A skin lesion imaged with a dermatoscope · a female subject in their 50s — 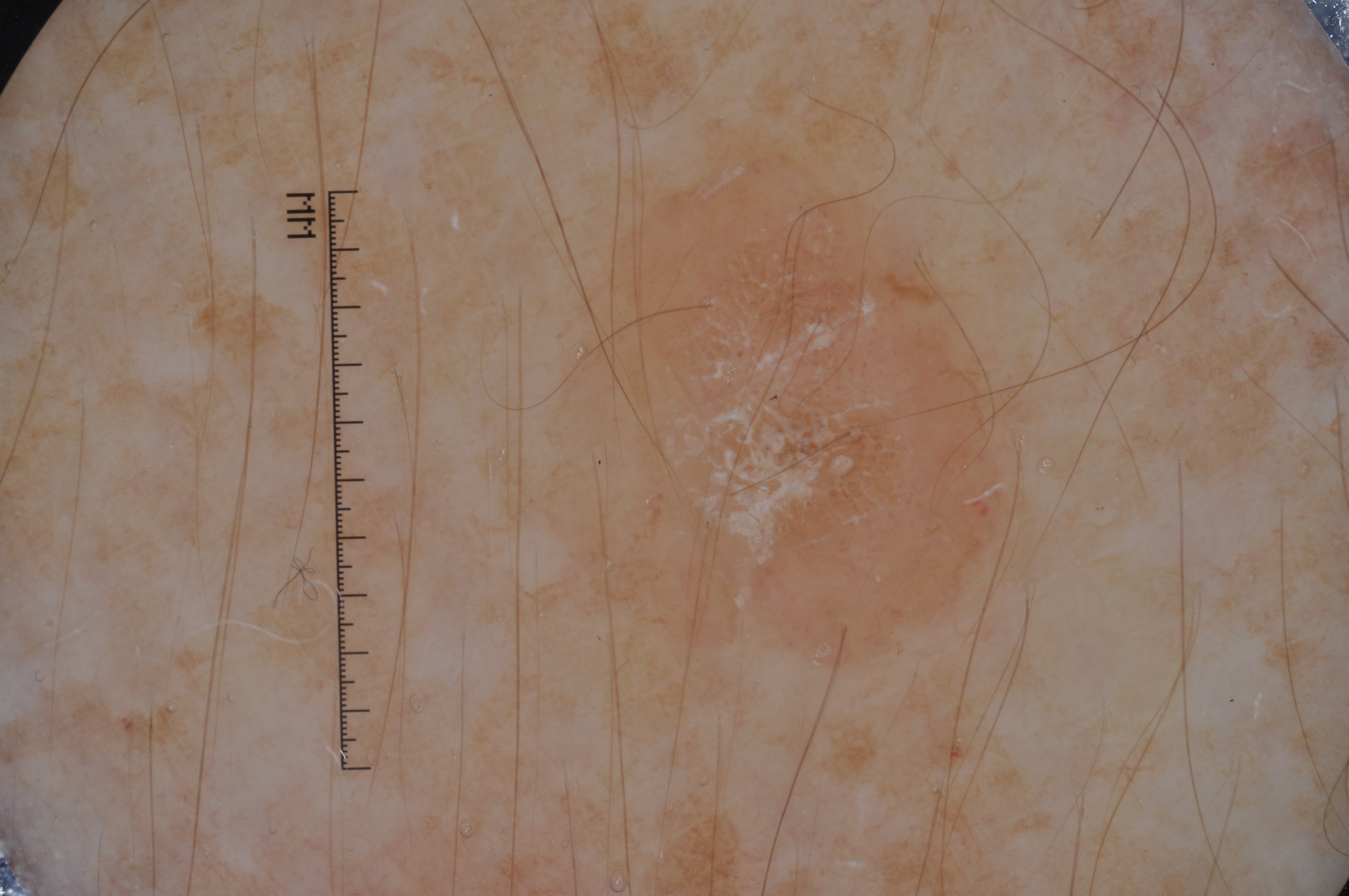Image and clinical context:
Dermoscopically, the lesion shows no streaks, pigment network, negative network, or milia-like cysts. The lesion is bounded by bbox=[569, 141, 1043, 665].
Assessment:
Diagnosed as a seborrheic keratosis.